A dermoscopic photograph of a skin lesion.
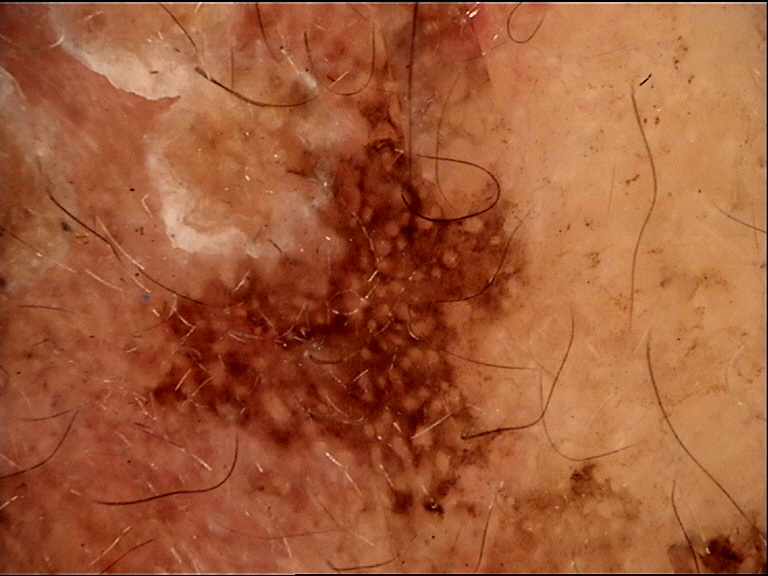{"lesion_type": {"main_class": "keratinocytic"}, "diagnosis": {"name": "seborrheic keratosis", "code": "sk", "malignancy": "benign", "super_class": "non-melanocytic", "confirmation": "expert consensus"}}